A dermoscopic view of a skin lesion.
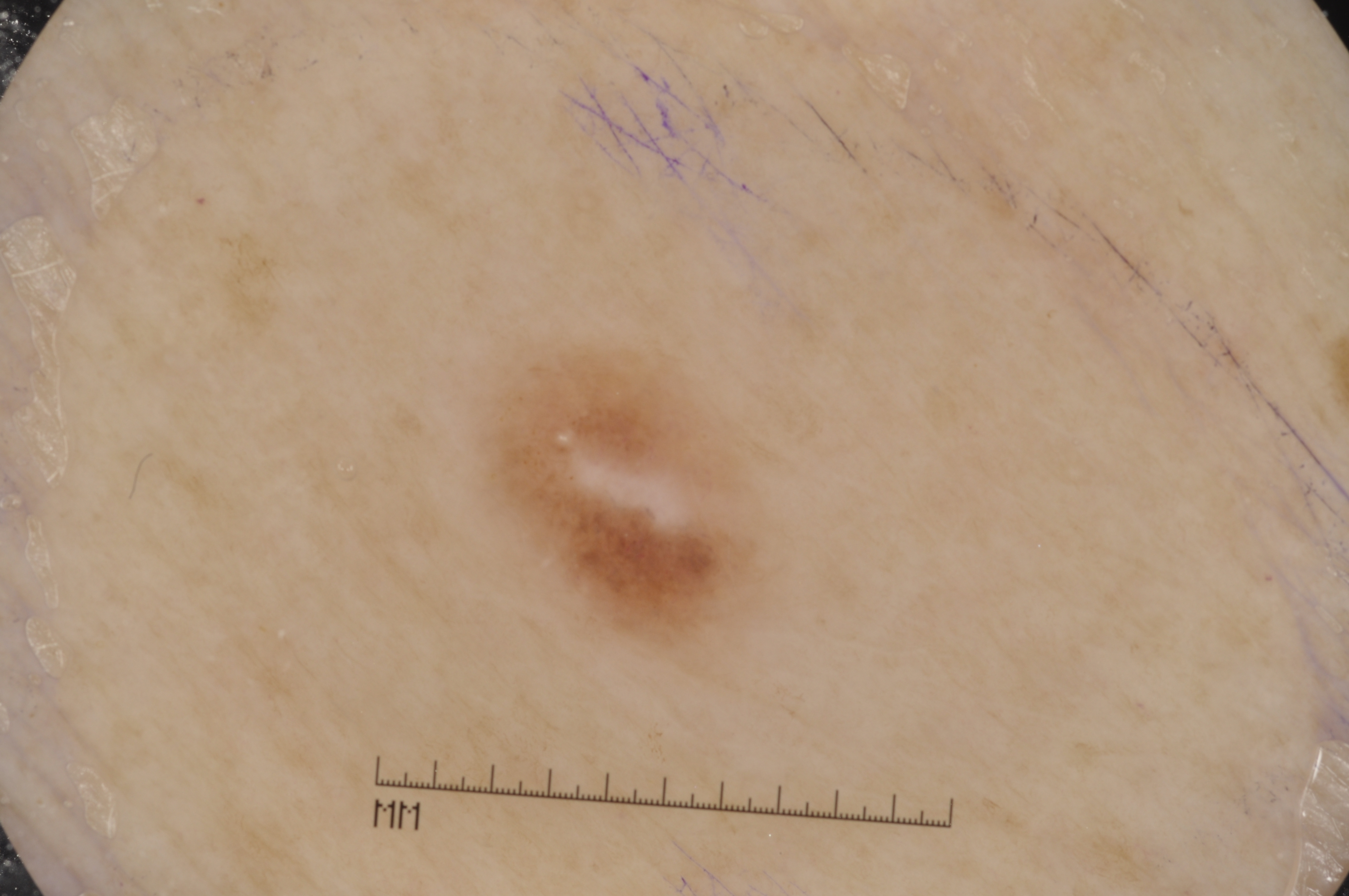| key | value |
|---|---|
| dermoscopic pattern | milia-like cysts; absent: pigment network, negative network, and streaks |
| bounding box | 474/348/776/654 |
| lesion size | small |
| impression | a melanocytic nevus |